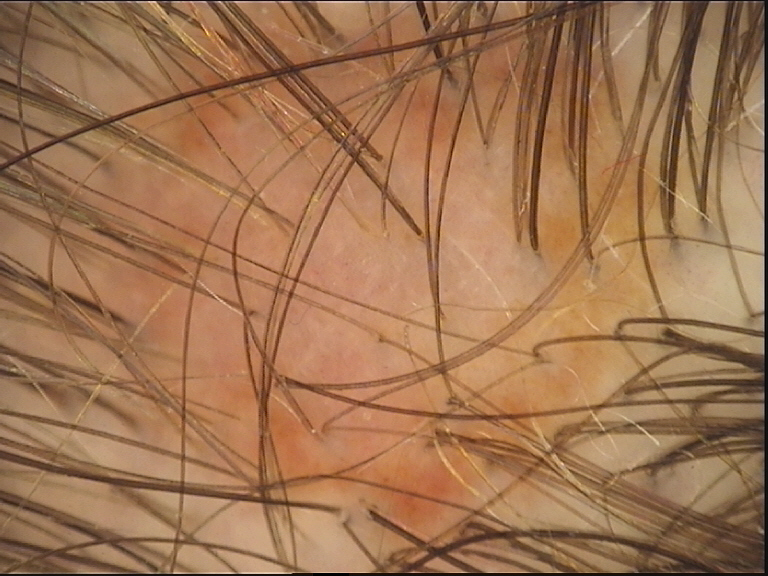Findings:
A skin lesion imaged with a dermatoscope. This is a banal lesion.
Impression:
The diagnostic label was a compound nevus.